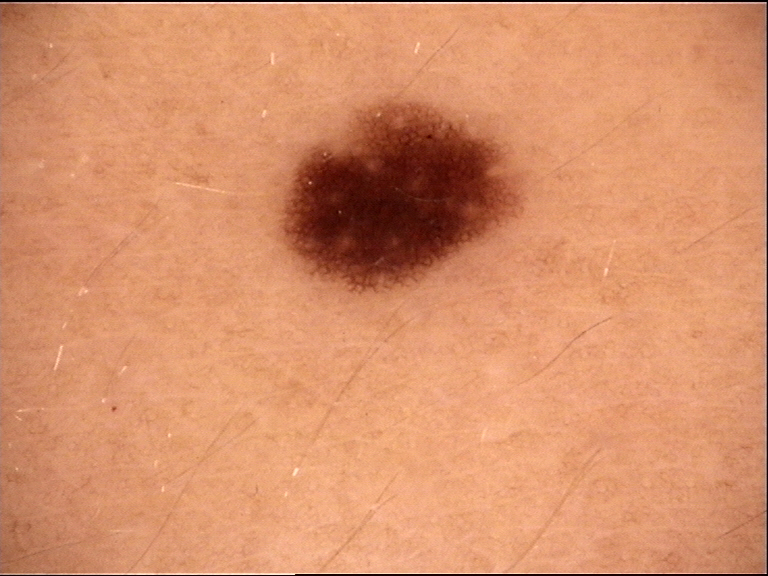Impression: Classified as a junctional nevus.